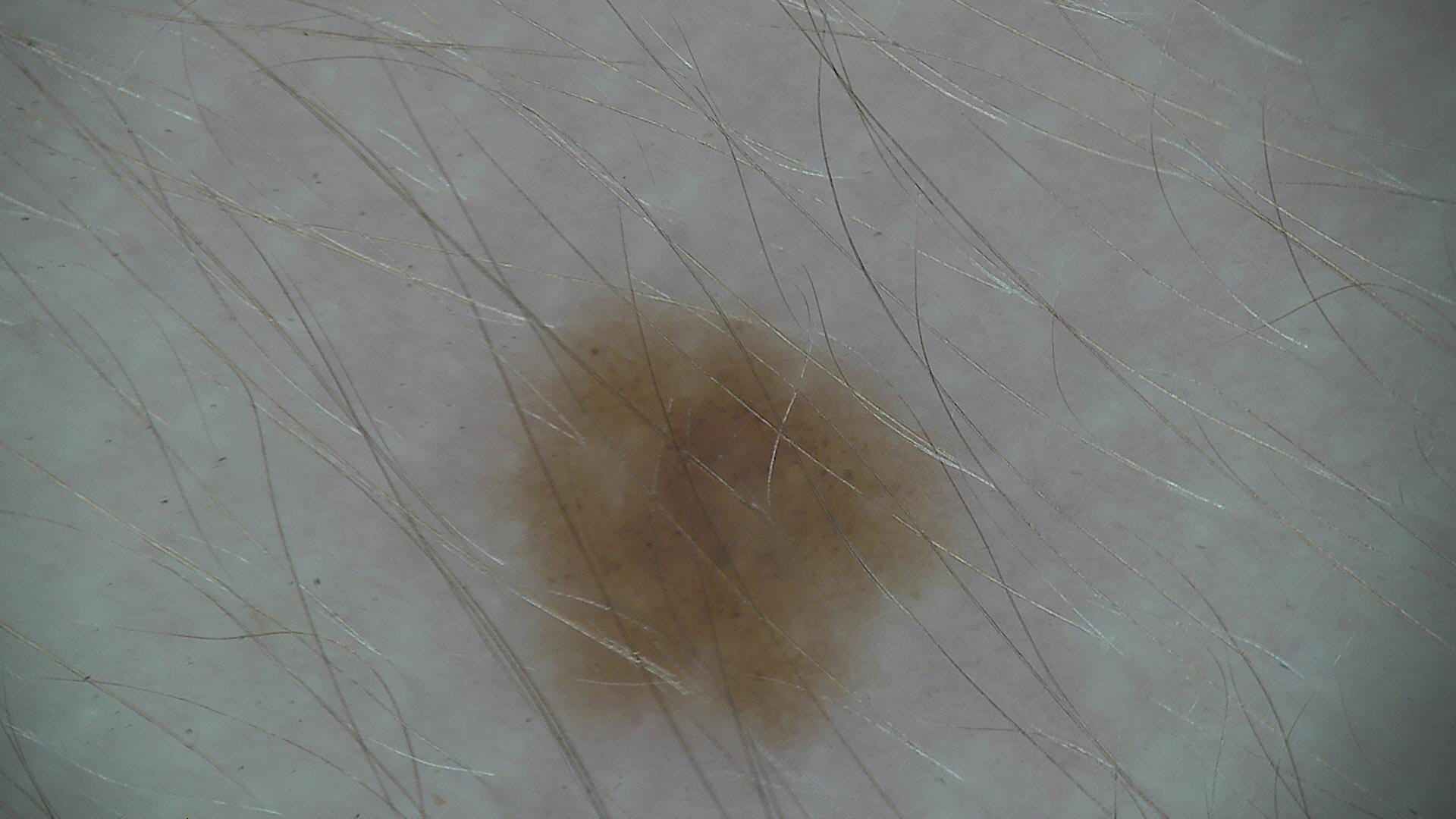label = dysplastic junctional nevus (expert consensus).